Female subject, age 60–69; the photograph was taken at a distance; no associated systemic symptoms reported; the arm is involved.
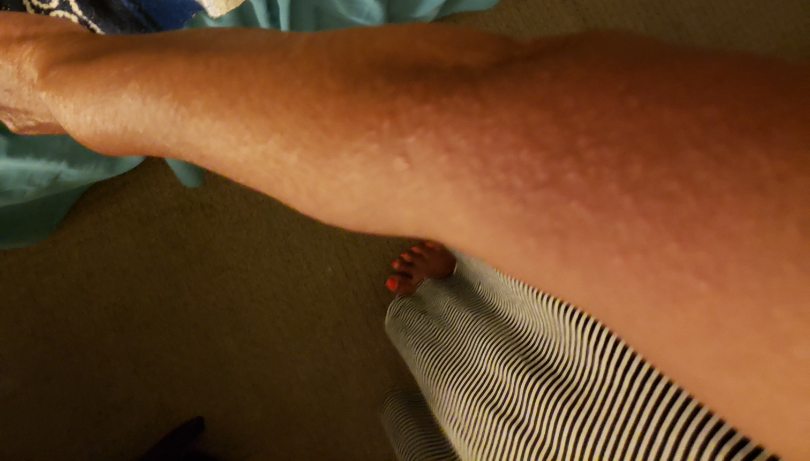| field | value |
|---|---|
| assessment | reviewed remotely by three dermatologists: Viral Exanthem, Hypersensitivity and Allergic Contact Dermatitis were each considered, in no particular order |